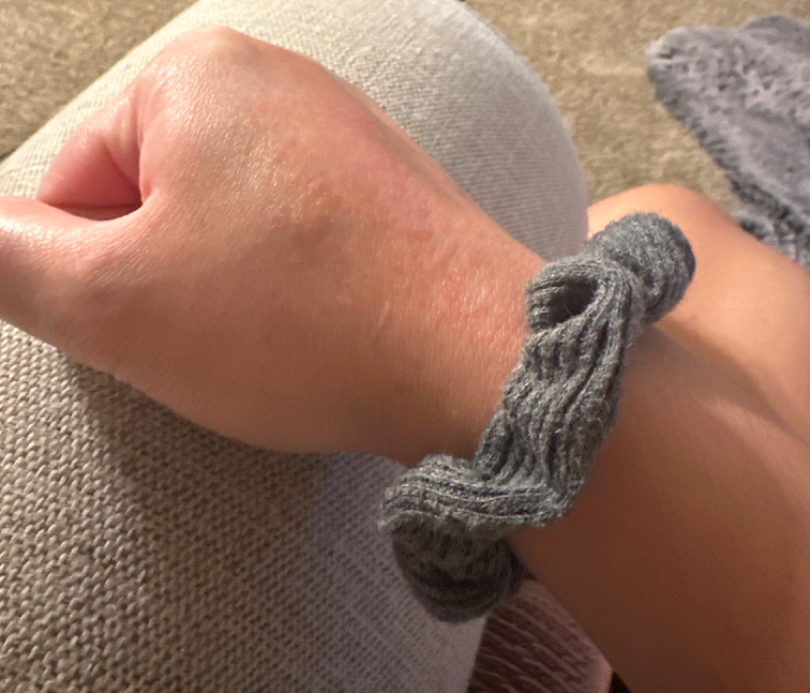The back of the hand is involved. Female subject, age 30–39. Fitzpatrick II; lay graders estimated Monk skin tone scale 4 (US pool) or 2 (India pool). The patient described the issue as a rash. This image was taken at an angle. Reported duration is about one day. On remote review of the image: most likely Lichen nitidus; possibly Eczema.